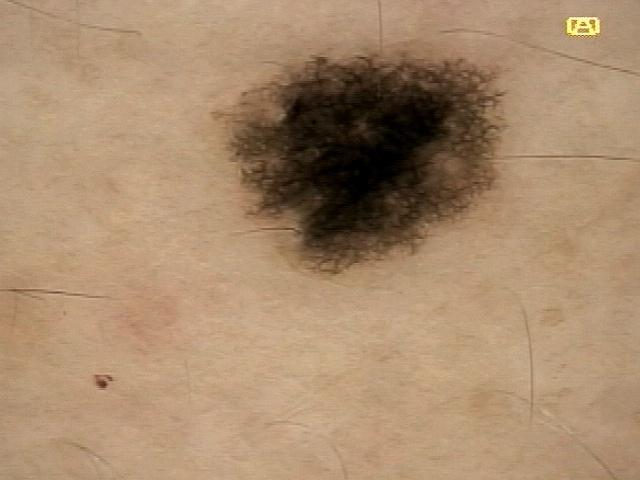Q: What did the workup show?
A: Nevus (biopsy-proven)